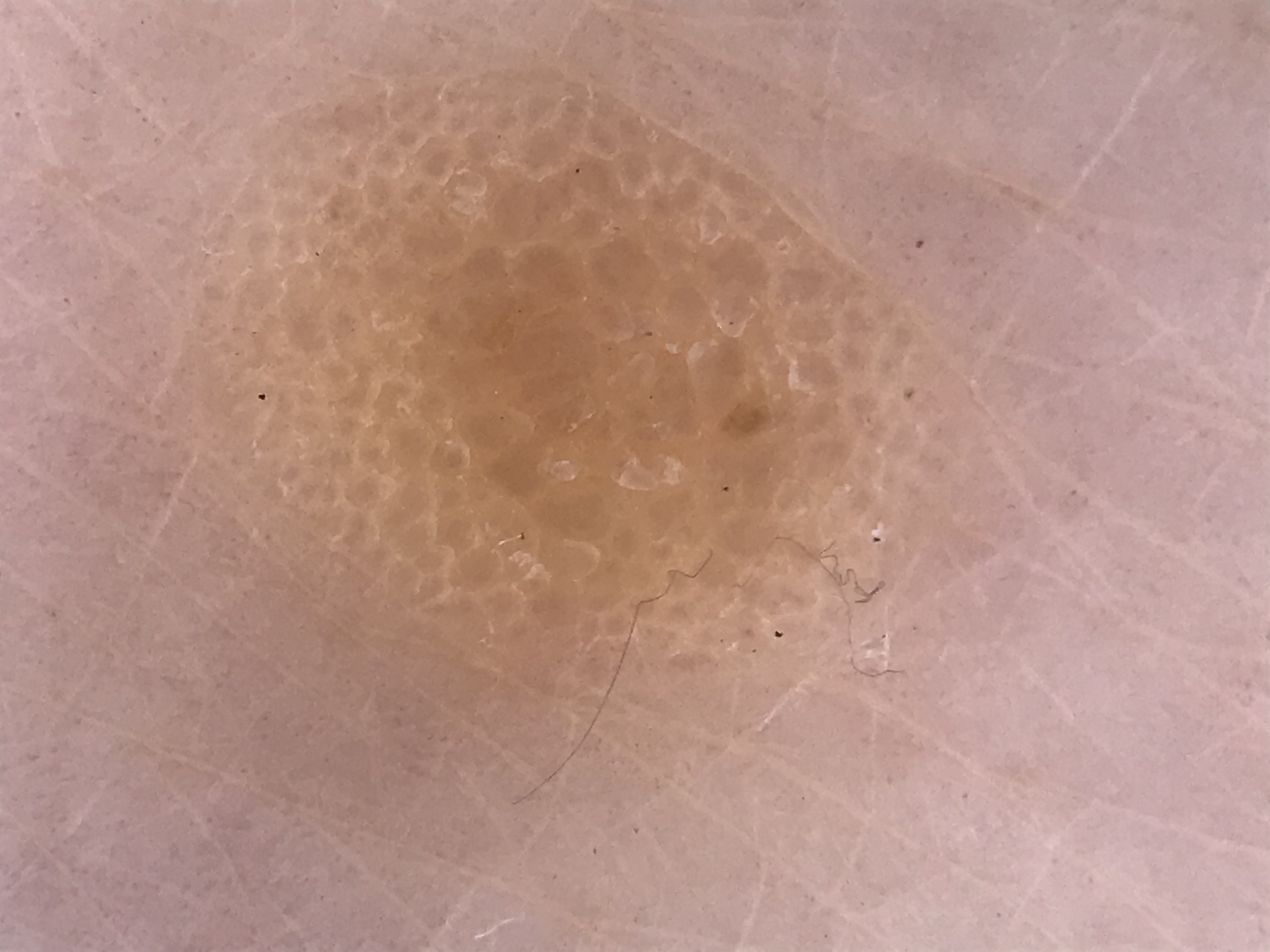Labeled as a seborrheic keratosis.